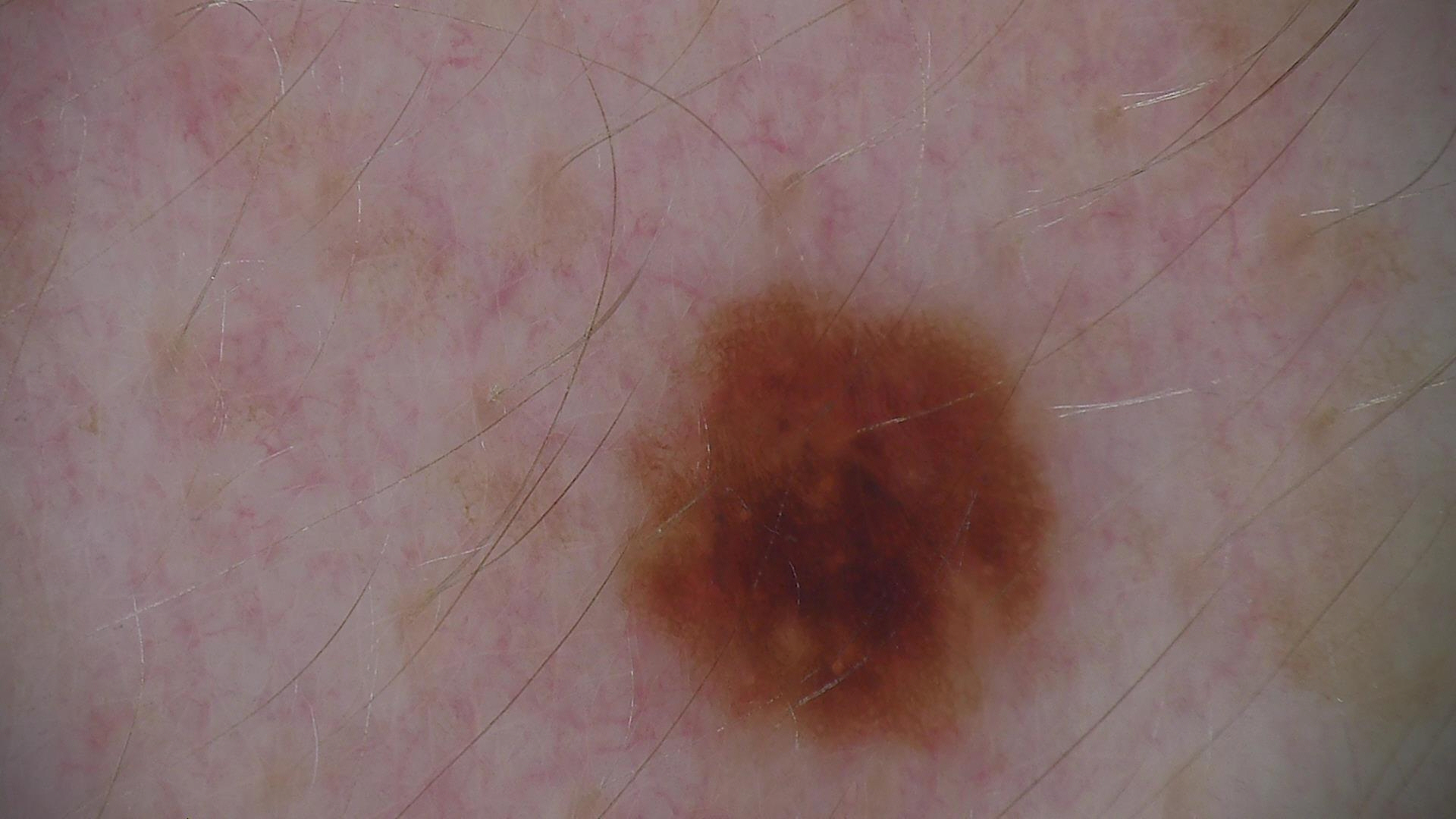Consistent with a dysplastic compound nevus.